A dermoscopy image of a single skin lesion: 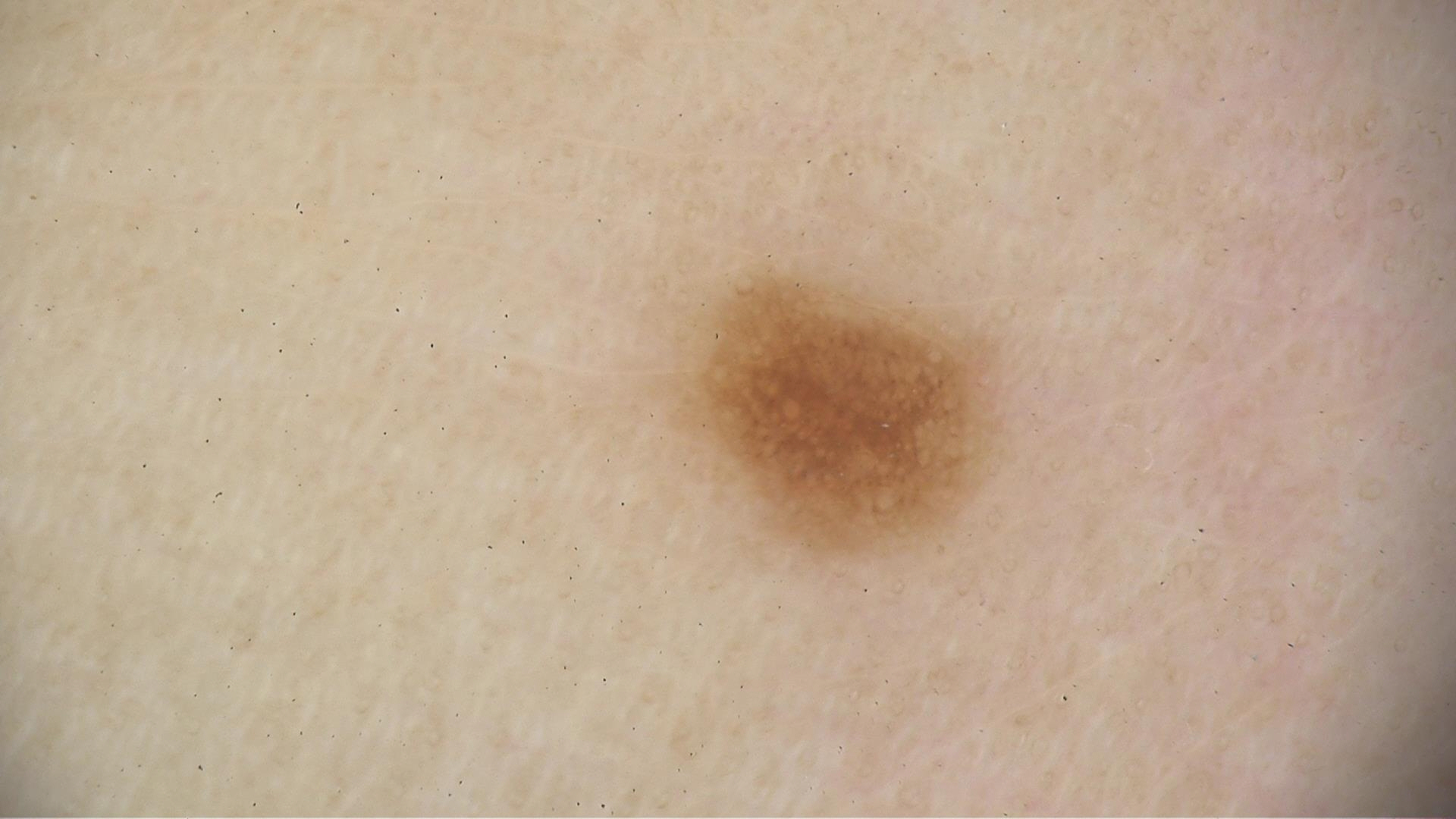Conclusion:
Labeled as a dysplastic junctional nevus.